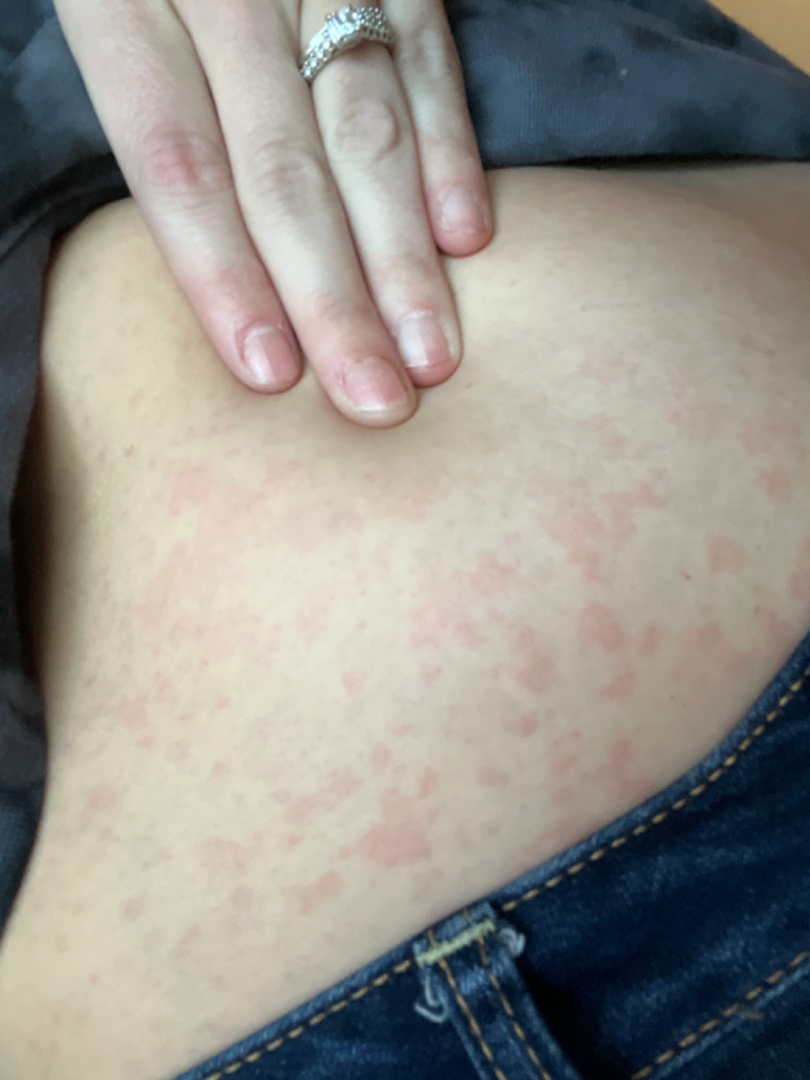surface texture: raised or bumpy
photo taken: at a distance
lesion symptoms: itching, pain and bothersome appearance
symptom duration: less than one week
location: front of the torso, back of the torso and leg
other reported symptoms: fatigue
patient's own categorization: a rash
assessment: Hypersensitivity and Allergic Contact Dermatitis were each considered, in no particular order; less likely is Viral Exanthem